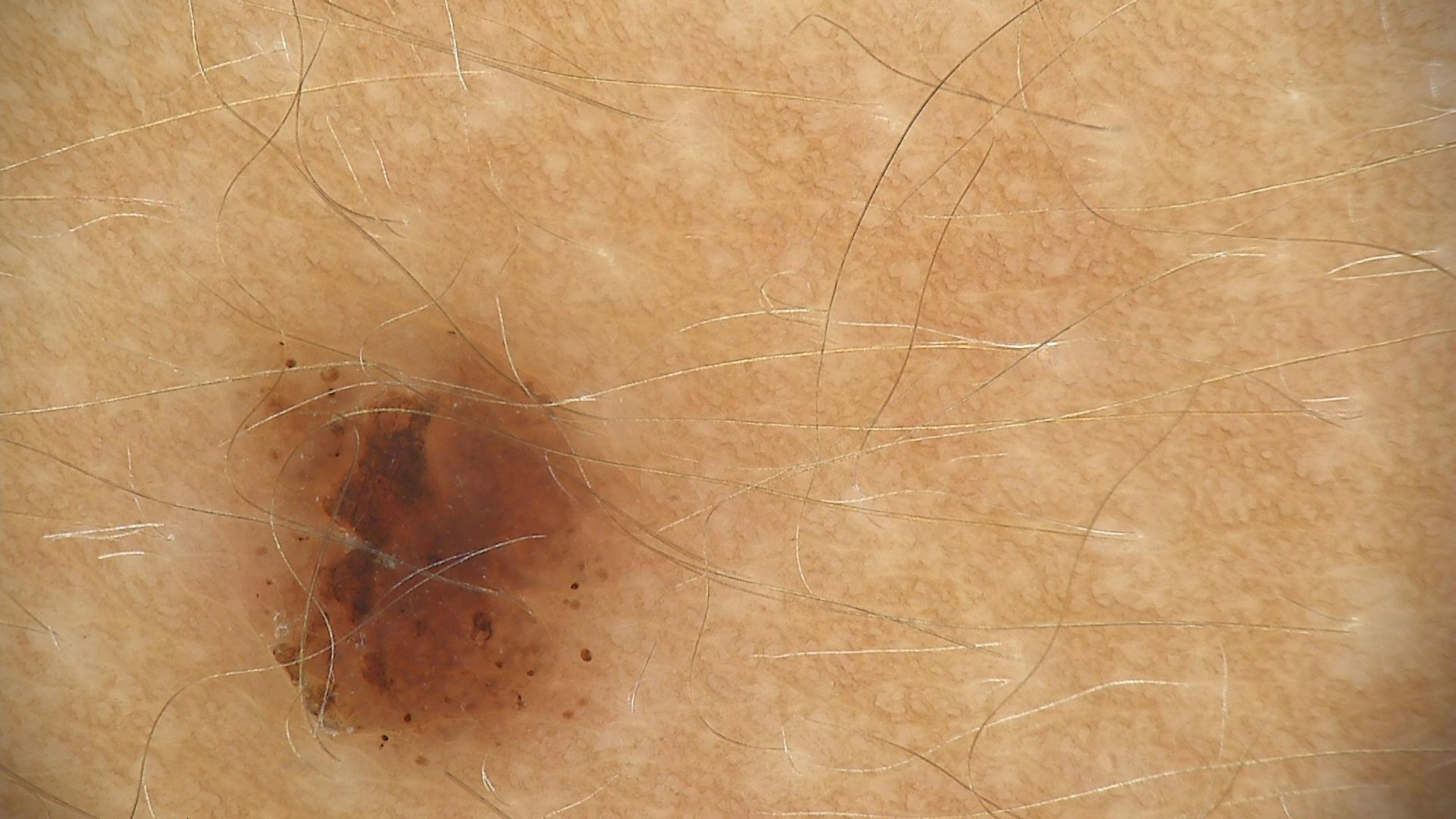imaging — dermatoscopy
assessment — dysplastic compound nevus (expert consensus)